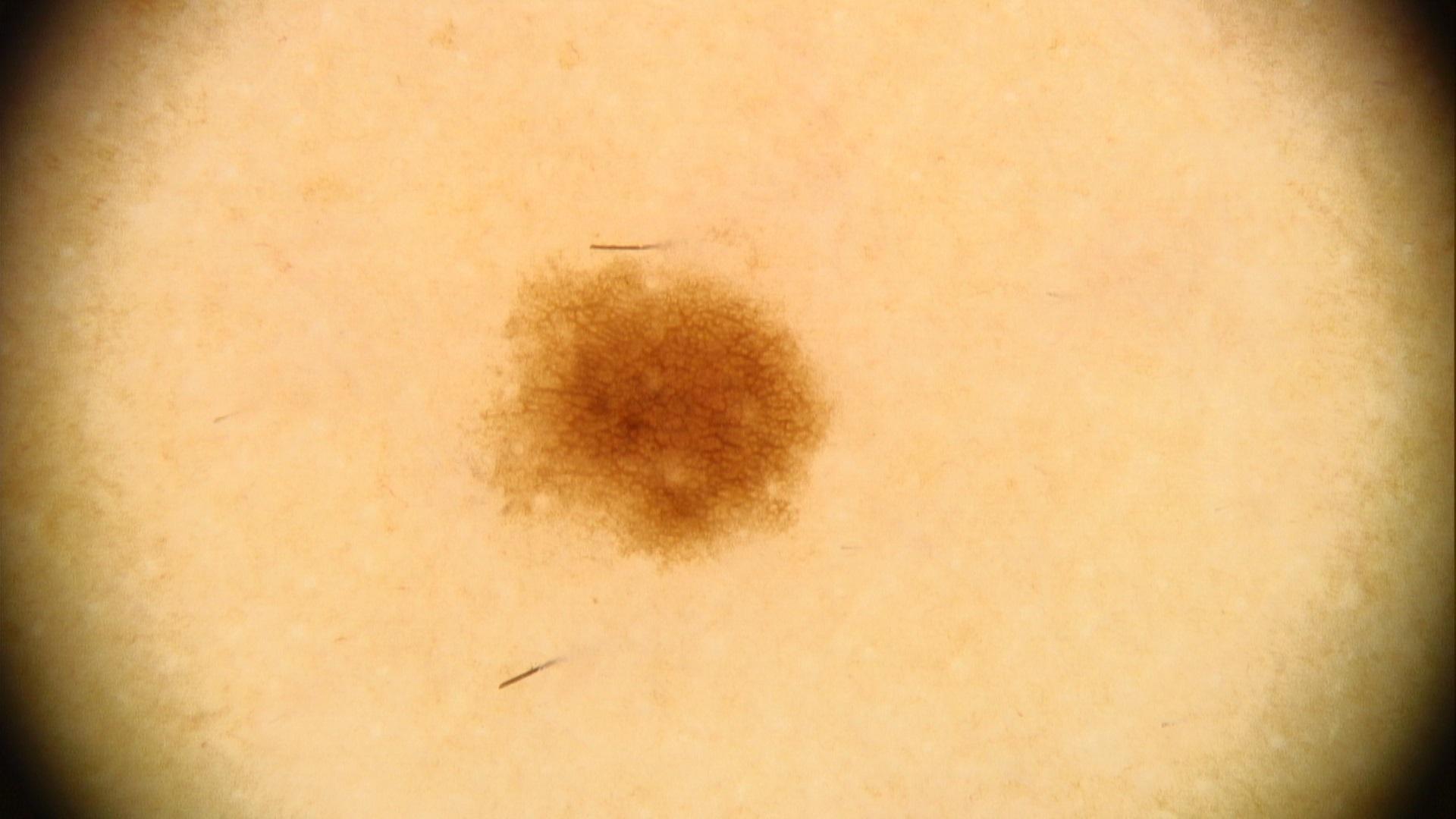Q: What was the clinical impression?
A: Nevus